A dermoscopic photograph of a skin lesion.
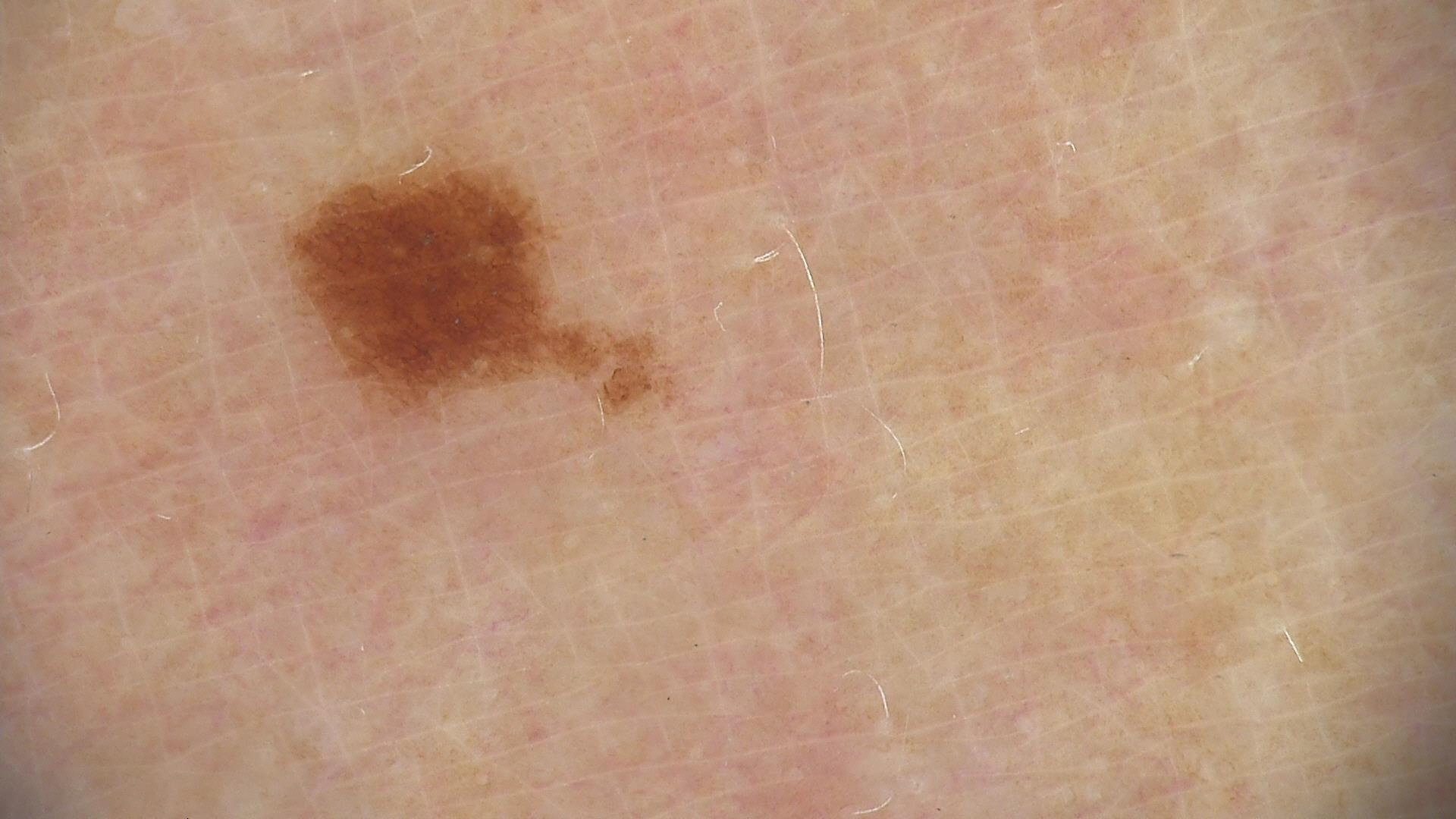class: dysplastic junctional nevus (expert consensus).